A female subject 92 years old. The patient says their skin tans without first burning. A clinical close-up of a skin lesion. On a questionnaire the patient reported a personal history of cancer and a family history of skin cancer. Imaged for a research study, with no referral diagnosis recorded.
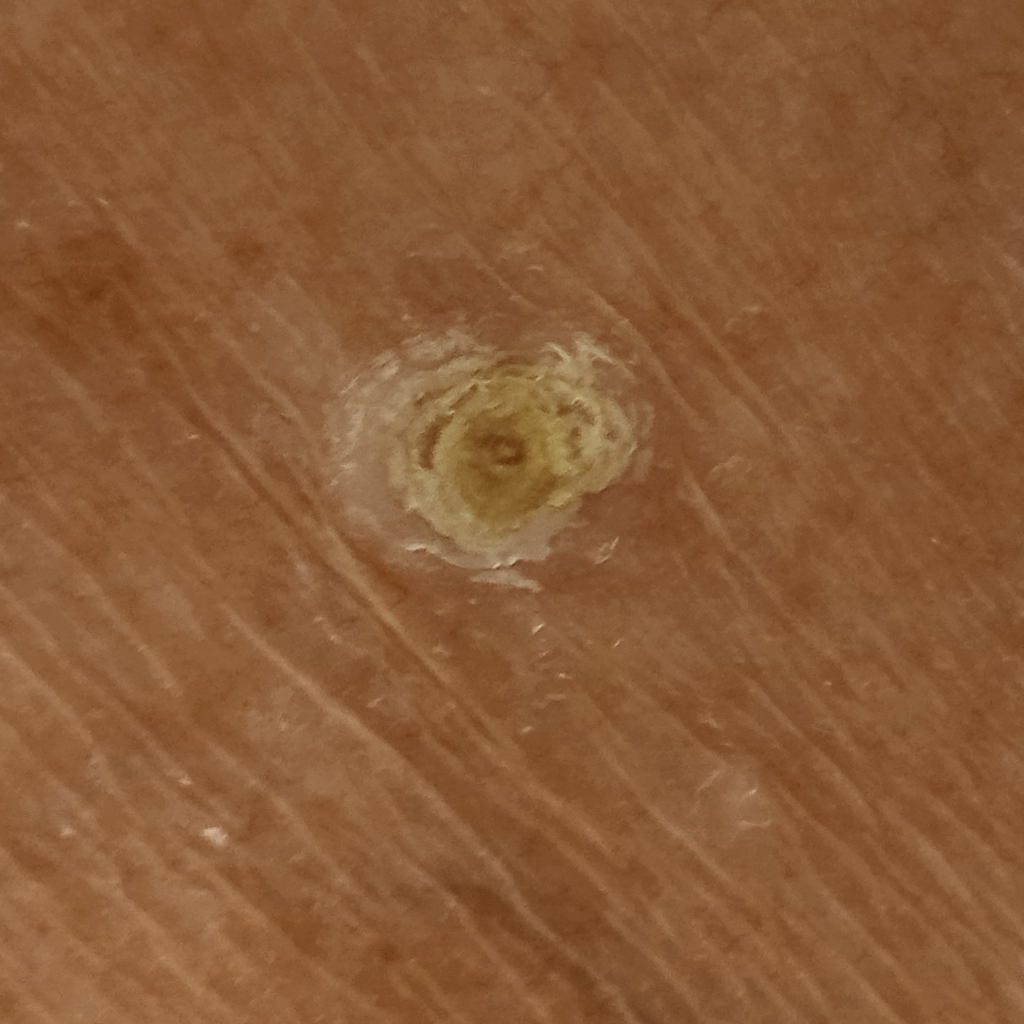– anatomic site · the torso
– diameter · 12.5 mm
– diagnosis · squamous cell carcinoma (dermatologist consensus)